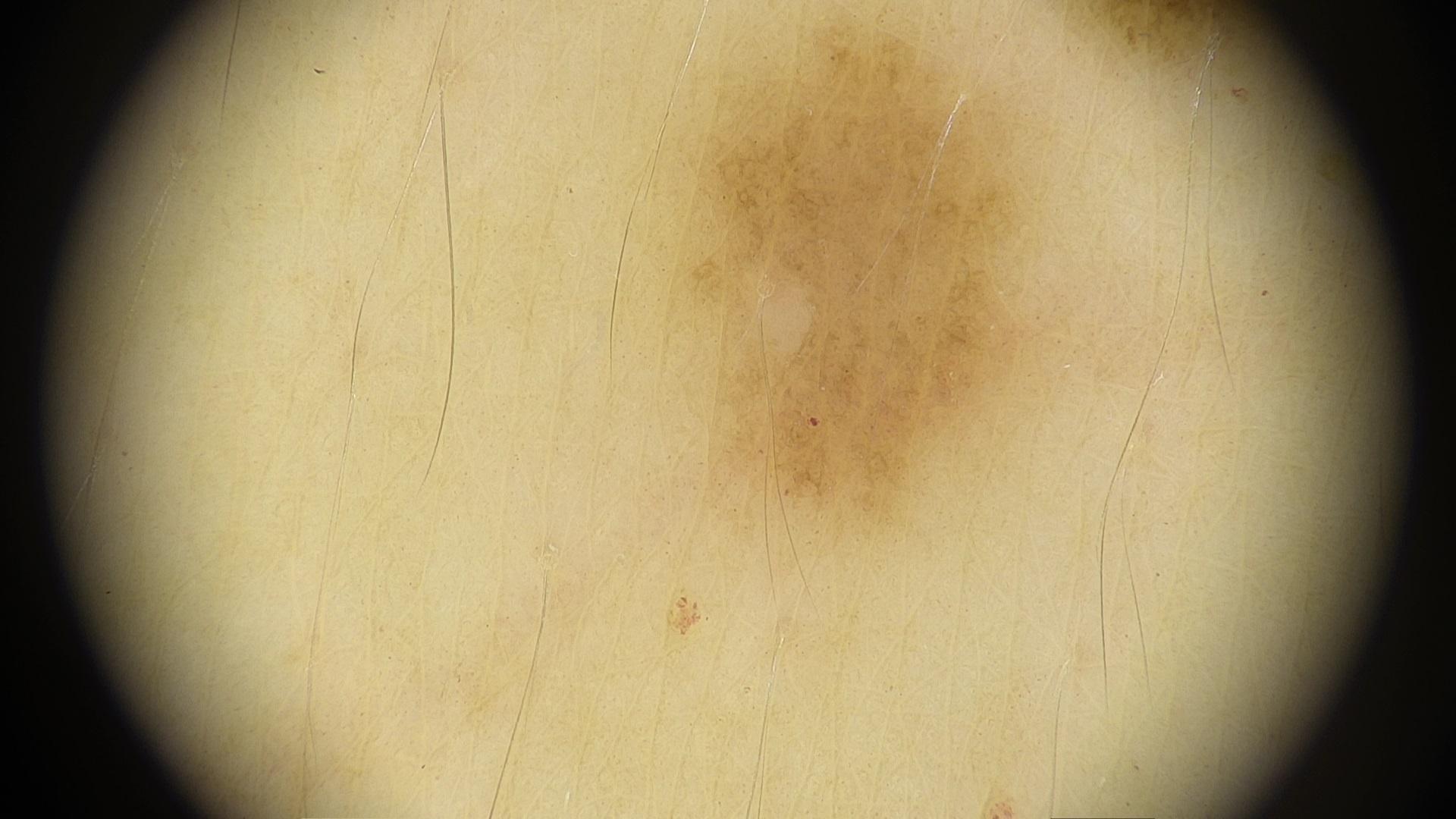Summary:
The patient is FST II. A female patient aged 33 to 37. A dermoscopic close-up of a skin lesion. The lesion involves the trunk.
Conclusion:
The diagnostic impression was a nevus.